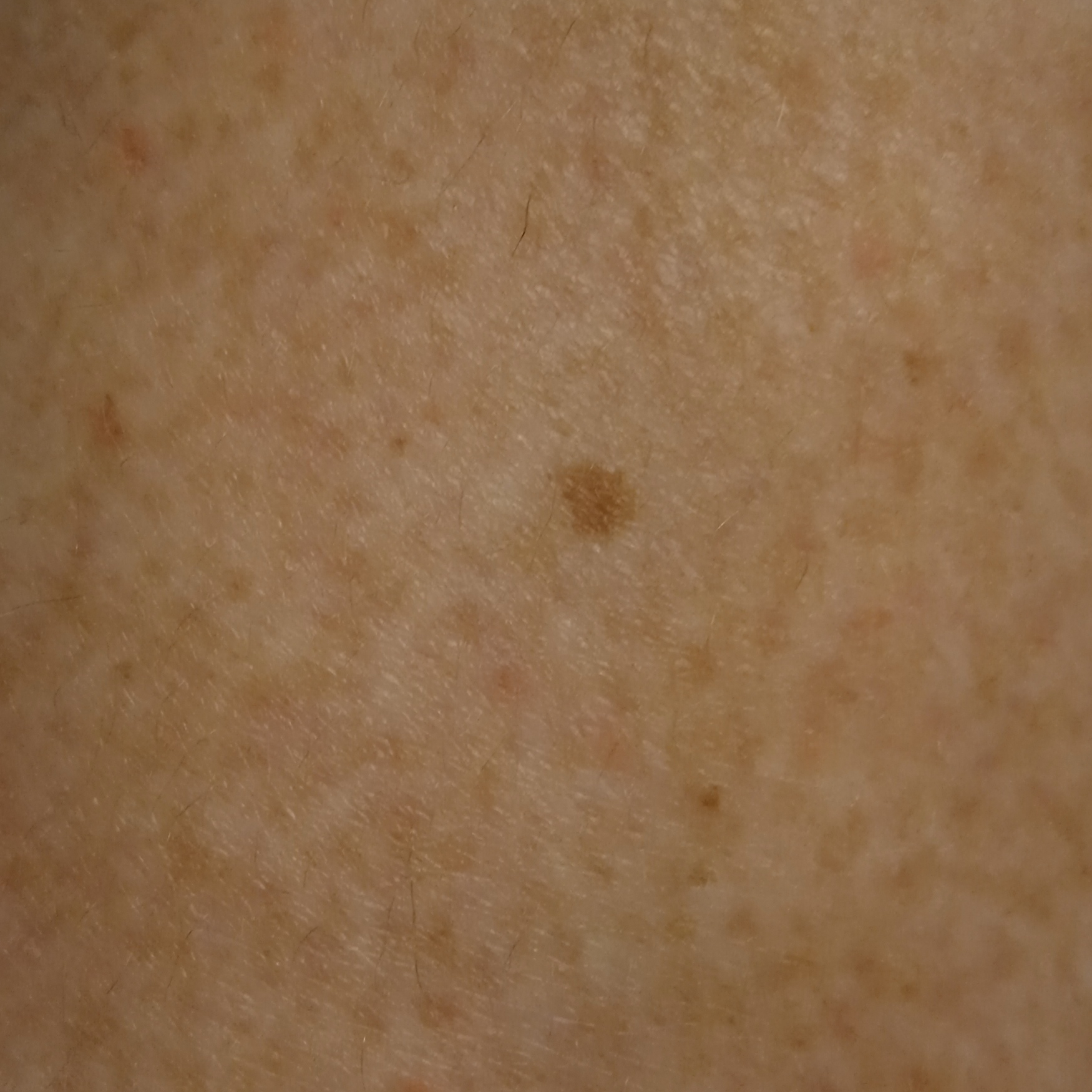  image: clinical photograph
  referral: research study (no referral diagnosis)
  mole_burden: a moderate number of melanocytic nevi
  lesion_location: a leg
  diagnosis:
    name: melanocytic nevus
    malignancy: benign